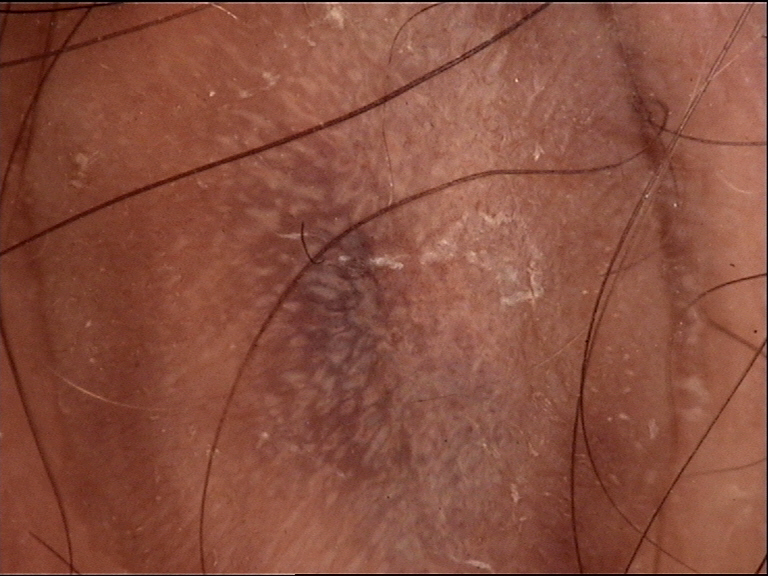Findings:
- diagnostic label · dermatofibroma (expert consensus)